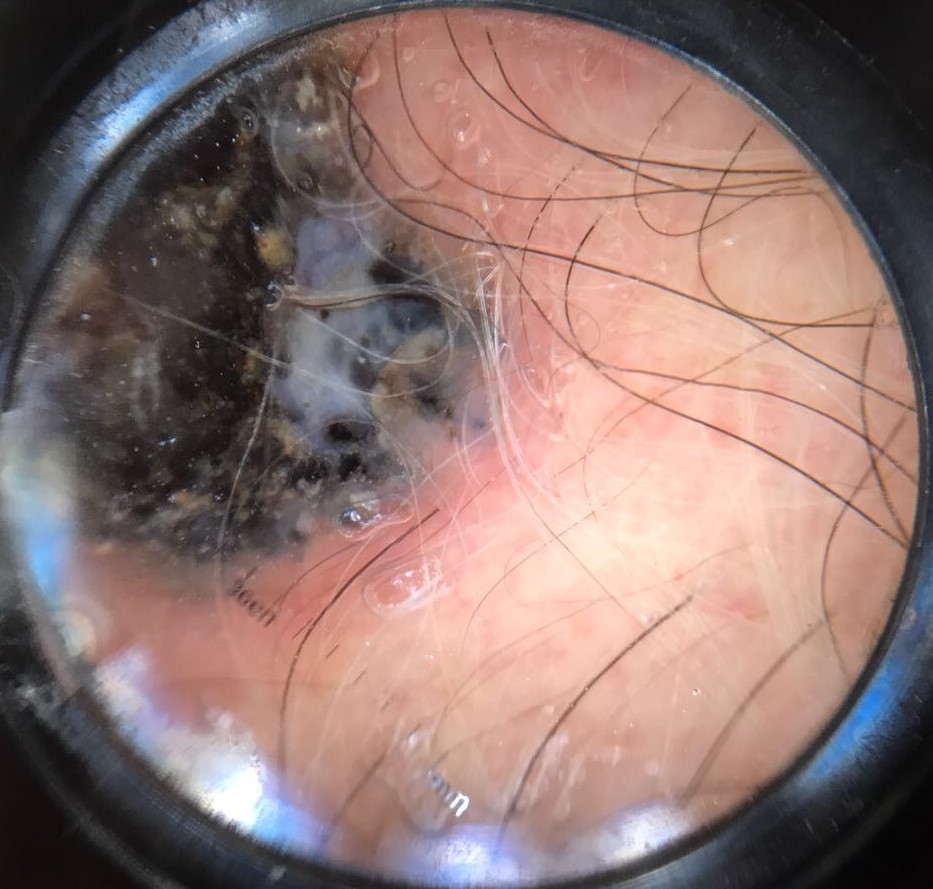A dermoscopic image of a skin lesion.
Biopsy-confirmed as a melanoma.